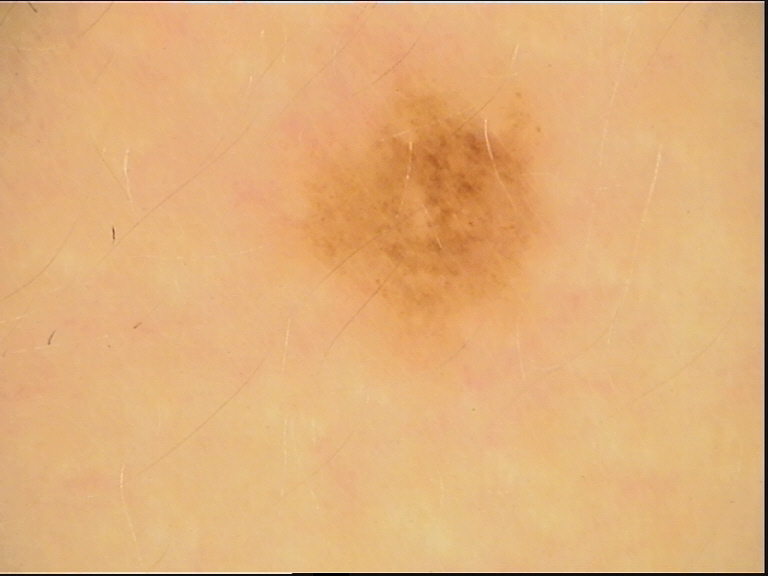Q: What is the imaging modality?
A: dermatoscopy
Q: What is this lesion?
A: dysplastic junctional nevus (expert consensus)